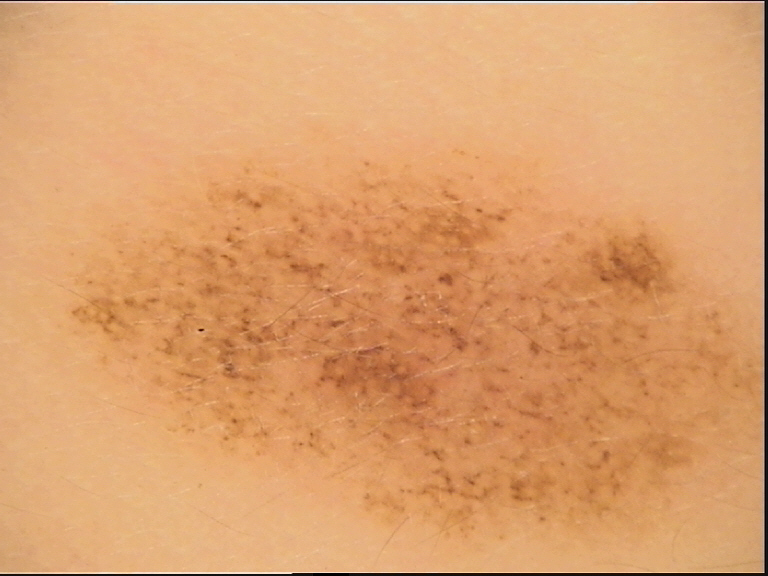A dermoscopic photograph of a skin lesion. Labeled as a dysplastic junctional nevus.